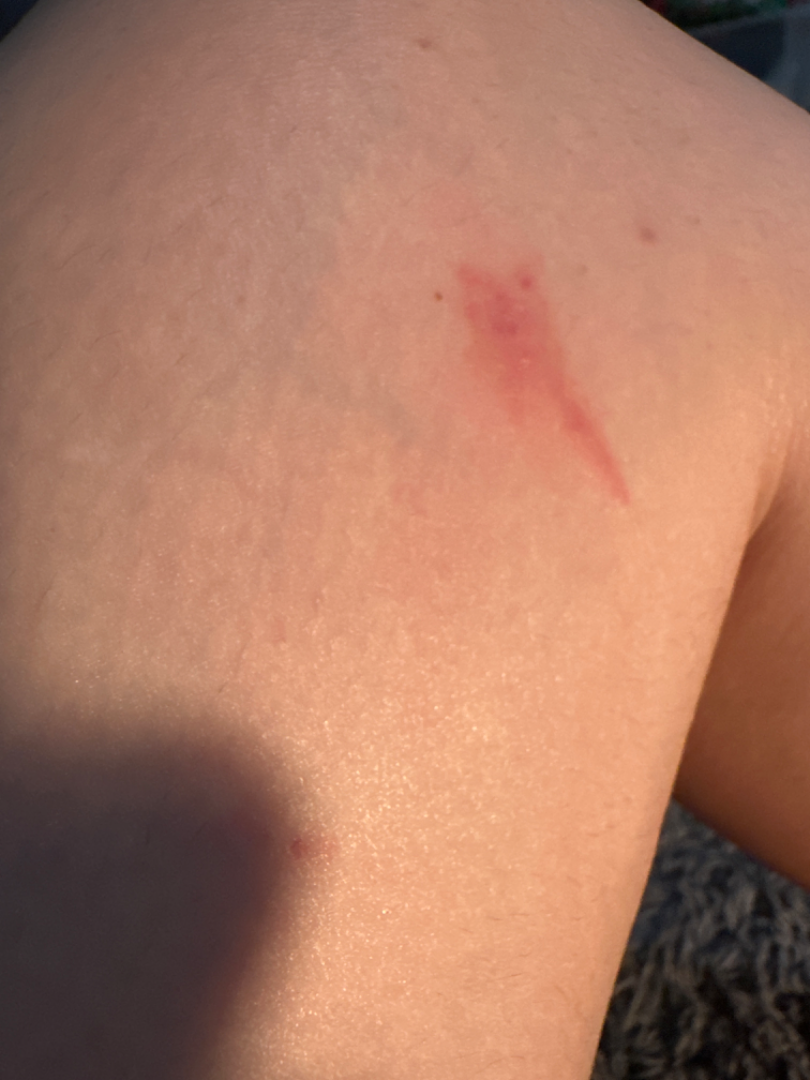Findings: The skin condition could not be confidently assessed from this image.